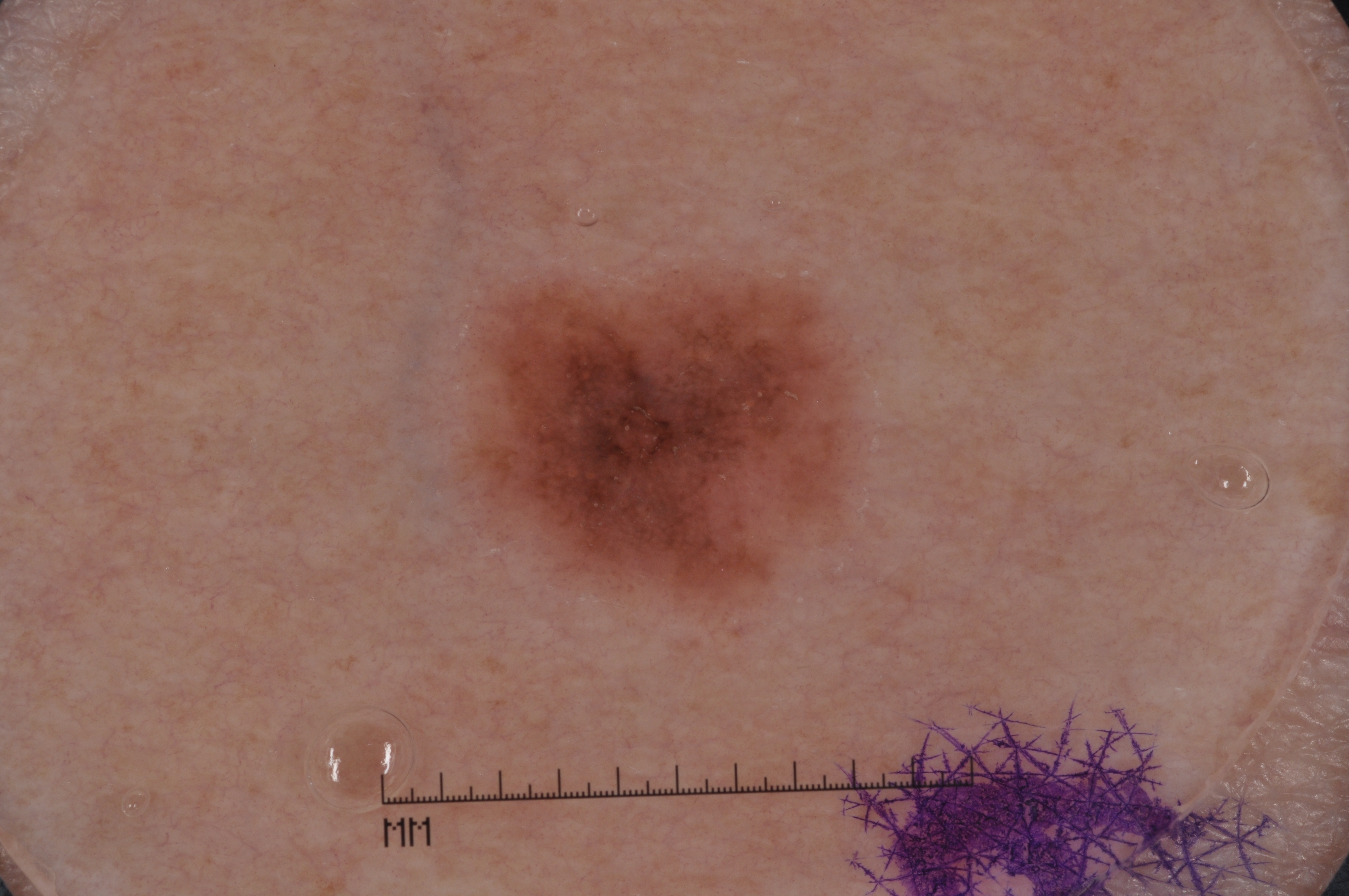<record>
<image>
  <modality>dermoscopy</modality>
</image>
<lesion_location>
  <bbox_xyxy>441, 253, 890, 630</bbox_xyxy>
</lesion_location>
<lesion_extent>moderate</lesion_extent>
<dermoscopic_features>
  <present>pigment network, milia-like cysts</present>
  <absent>streaks, negative network</absent>
</dermoscopic_features>
<diagnosis>
  <name>melanocytic nevus</name>
  <malignancy>benign</malignancy>
  <lineage>melanocytic</lineage>
  <provenance>clinical</provenance>
</diagnosis>
</record>